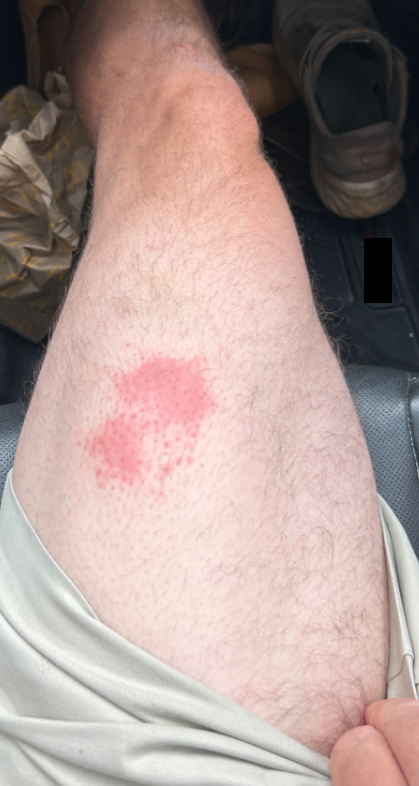Q: What was the assessment?
A: unable to determine
Q: What symptoms does the patient report?
A: bothersome appearance
Q: What is the framing?
A: at a distance
Q: Age and sex?
A: male, age 30–39
Q: Anatomic location?
A: leg
Q: How does the patient describe it?
A: a rash